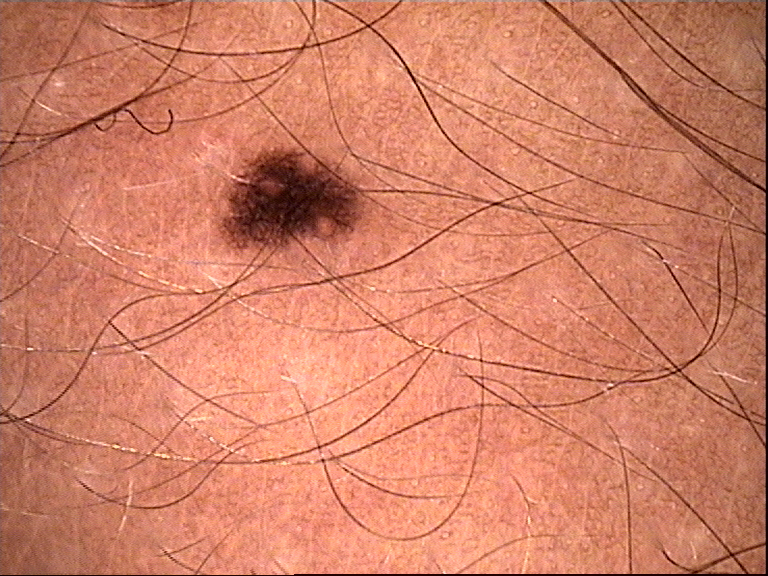A dermoscopic close-up of a skin lesion.
Diagnosed as a dysplastic junctional nevus.